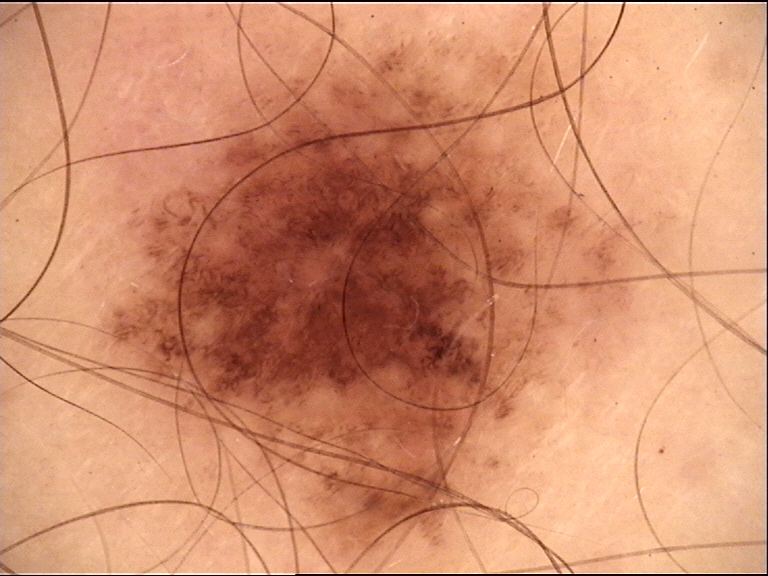<dermoscopy>
  <diagnosis>
    <name>dysplastic compound nevus</name>
    <code>cd</code>
    <malignancy>benign</malignancy>
    <super_class>melanocytic</super_class>
    <confirmation>expert consensus</confirmation>
  </diagnosis>
</dermoscopy>